A dermoscopic close-up of a skin lesion.
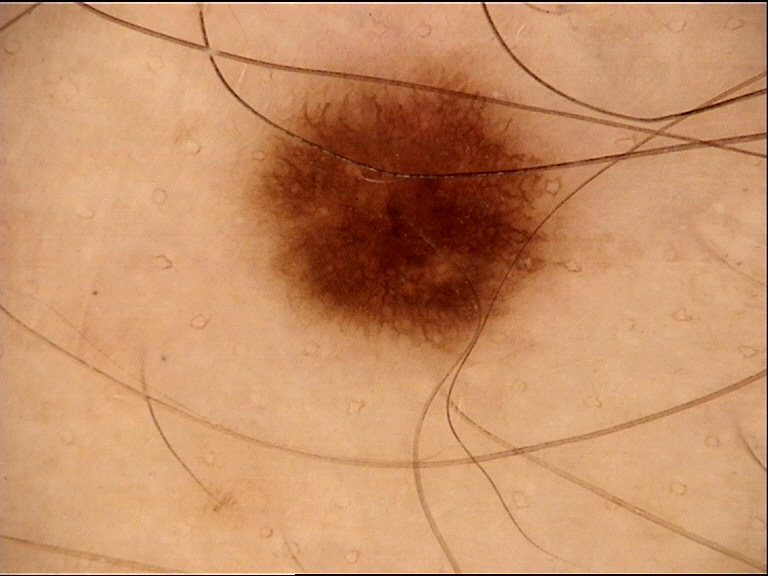Conclusion:
Consistent with a dysplastic junctional nevus.